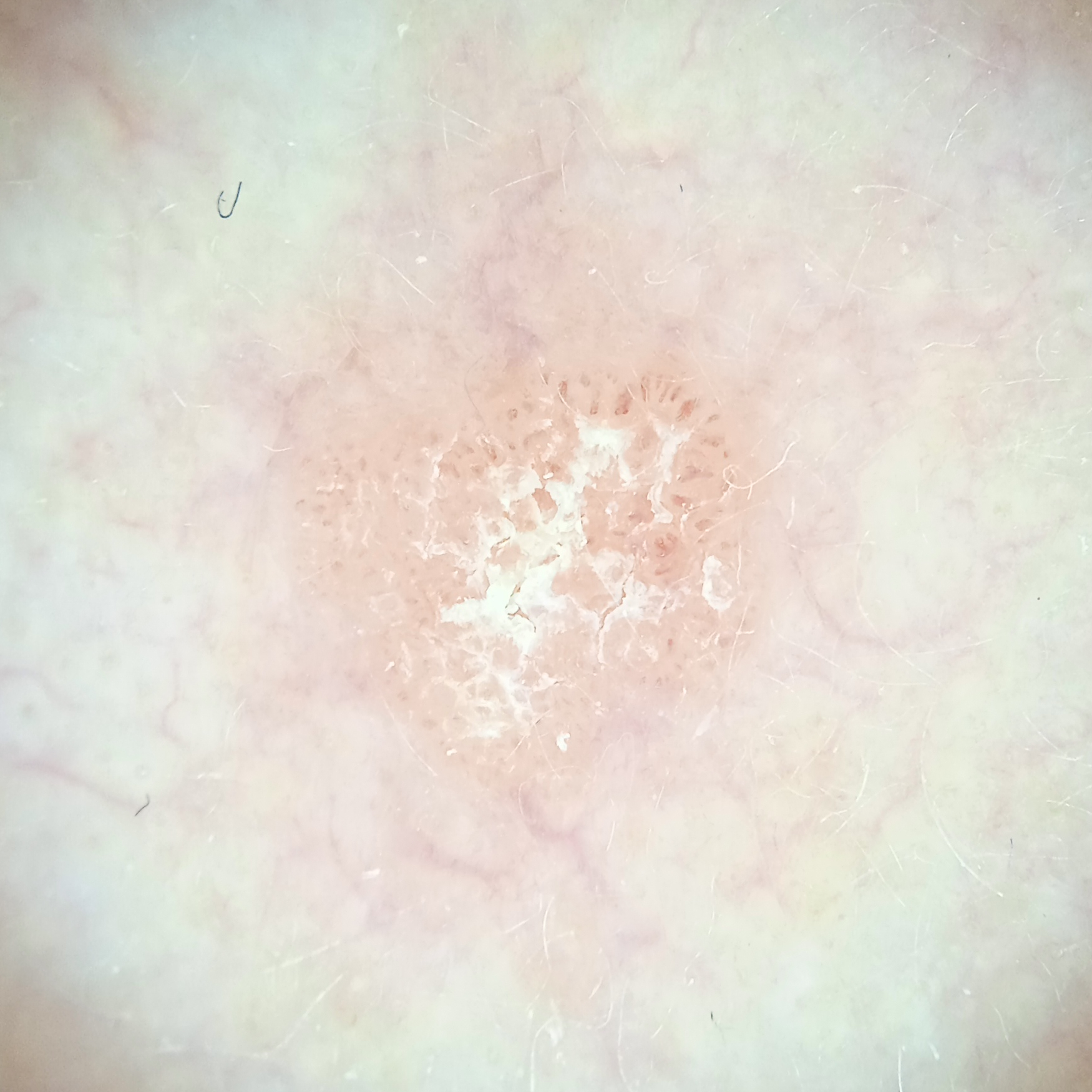Q: What was the diagnosis?
A: actinic keratosis (dermatologist consensus)